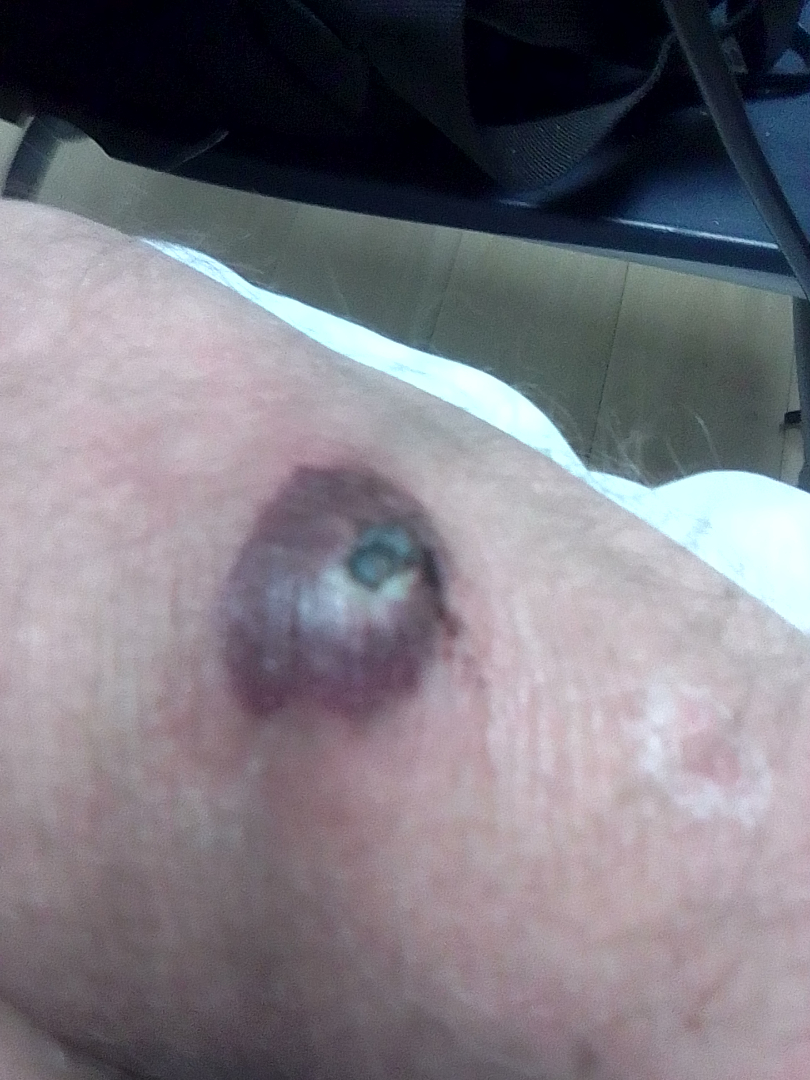Q: What was the assessment?
A: indeterminate from the photograph
Q: How was the photo taken?
A: close-up
Q: Anatomic location?
A: arm